The patient considered this a rash; a close-up photograph; the lesion involves the arm; the patient reports the lesion is raised or bumpy; reported lesion symptoms include itching, enlargement and bothersome appearance; the patient reports the condition has been present for about one day — 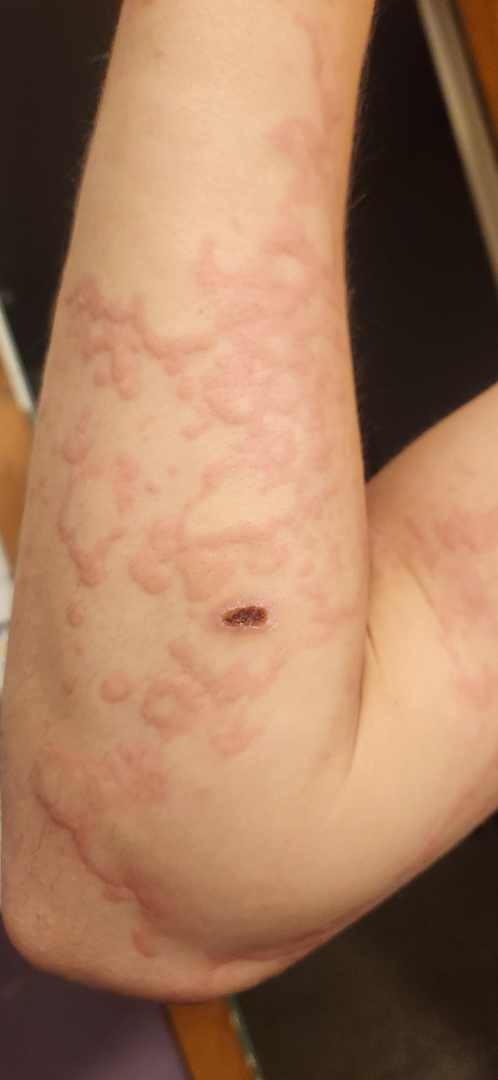Leukocytoclastic Vasculitis (weight 0.54); Calciphylaxis cutis (weight 0.23); Erythema multiforme (weight 0.23).